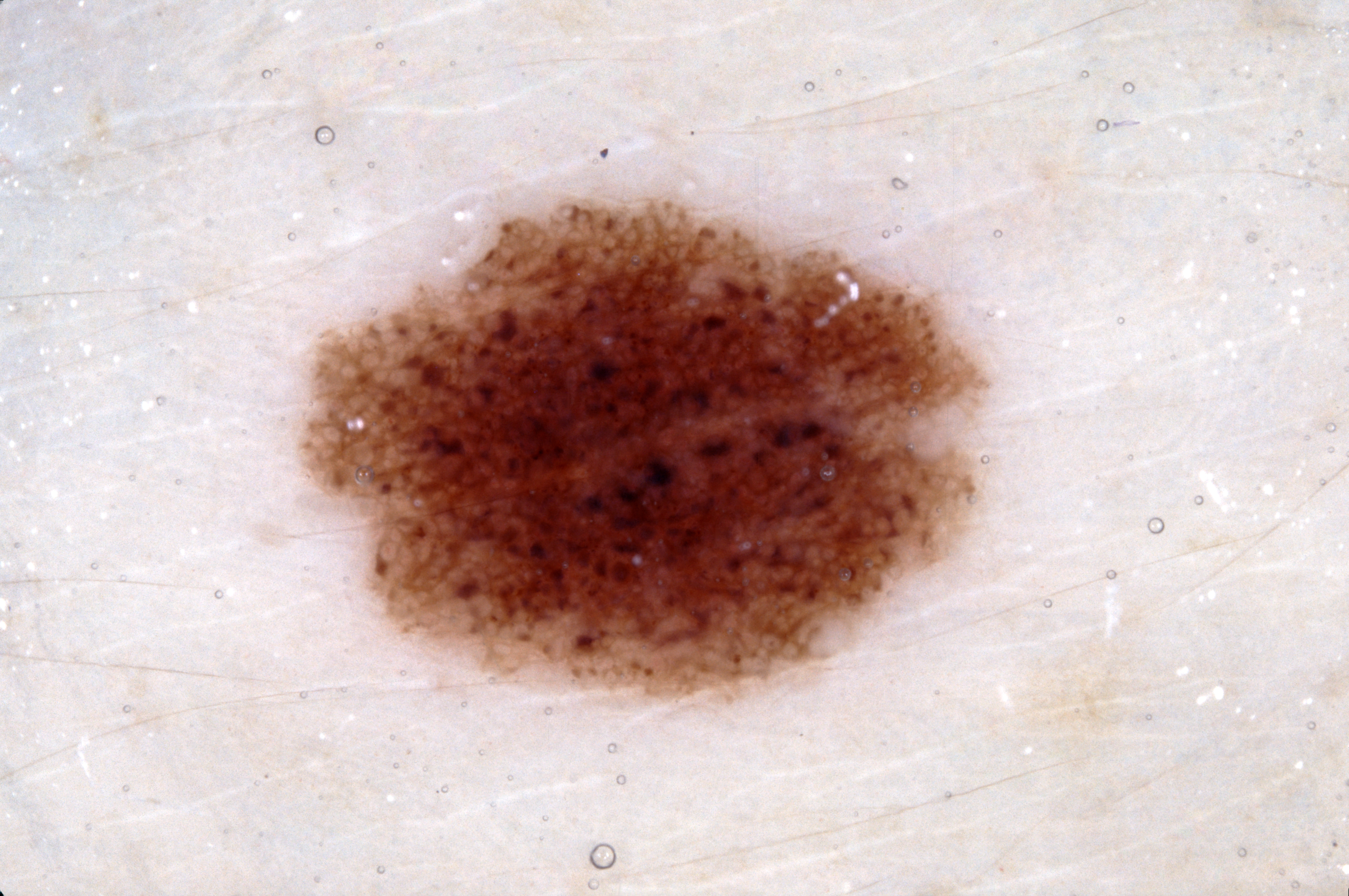Image and clinical context: A dermoscopy image of a single skin lesion. A female subject, approximately 30 years of age. The lesion is located at x1=291 y1=177 x2=999 y2=718. Dermoscopic examination shows pigment network. Impression: The lesion was assessed as a melanocytic nevus.